A dermoscopy image of a single skin lesion.
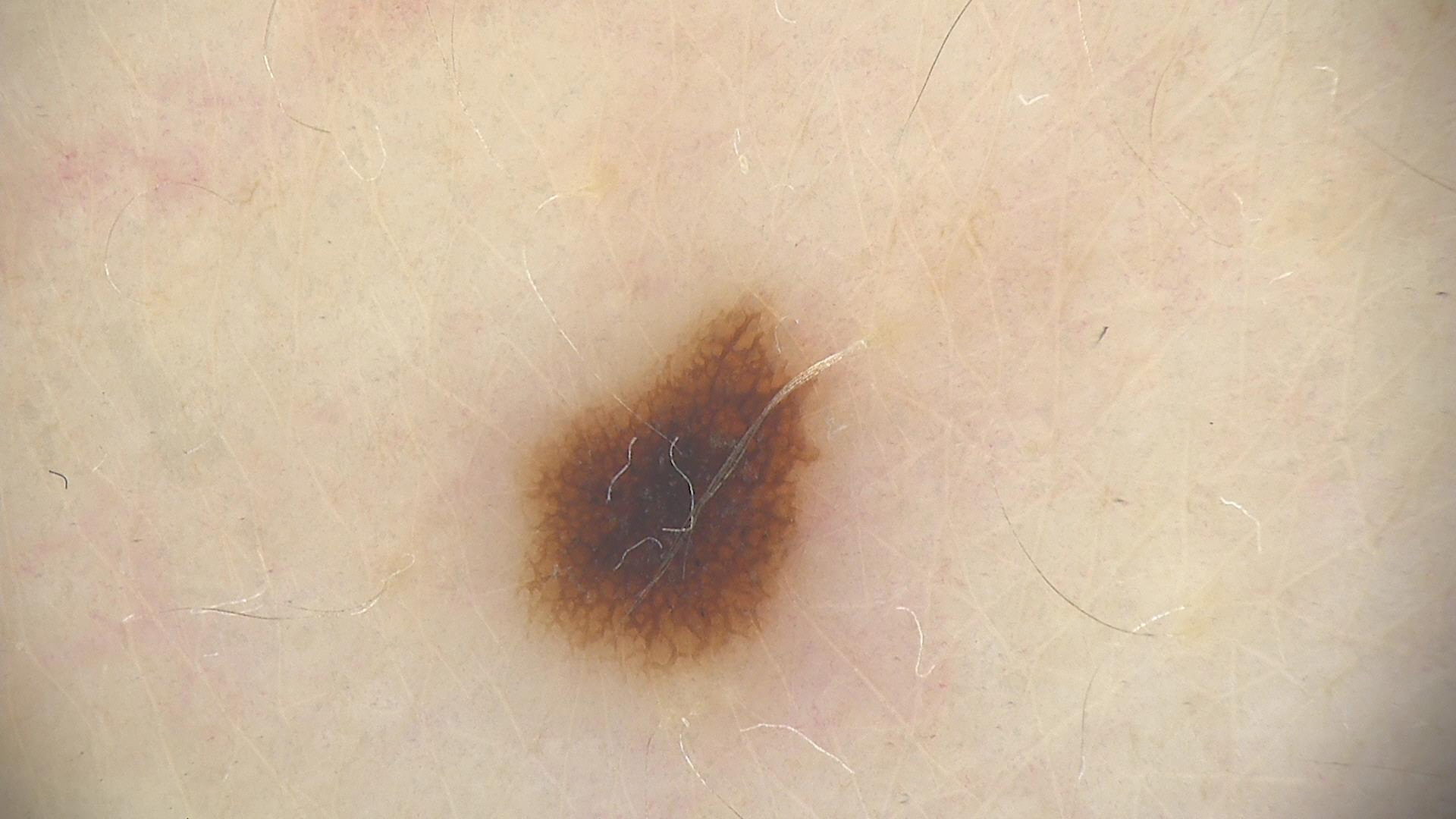Q: What is this lesion?
A: dysplastic junctional nevus (expert consensus)